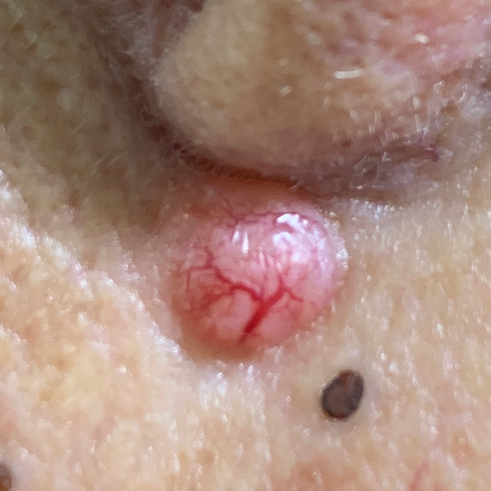| feature | finding |
|---|---|
| image type | clinical photograph |
| subject | female, age 78 |
| risk factors | prior skin cancer (patient or family) |
| skin type | III |
| site | the face |
| pathology | basal cell carcinoma (biopsy-proven) |